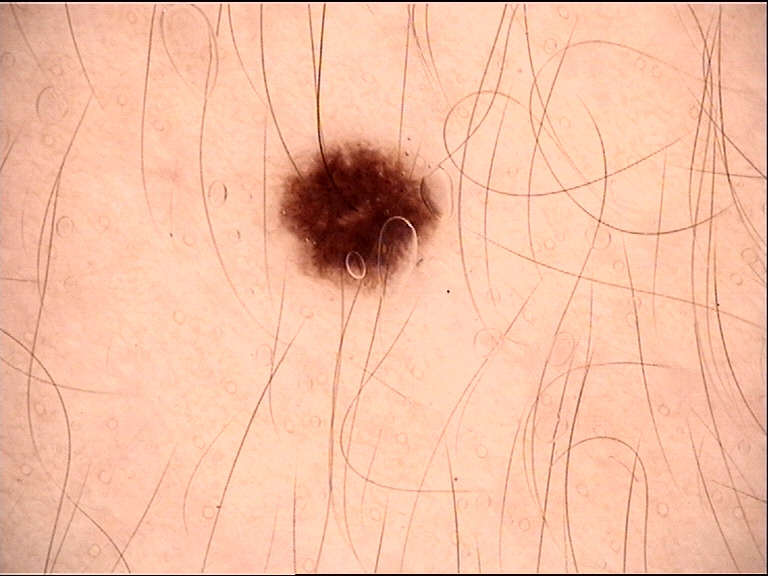Classified as a junctional nevus.